Close-up view: 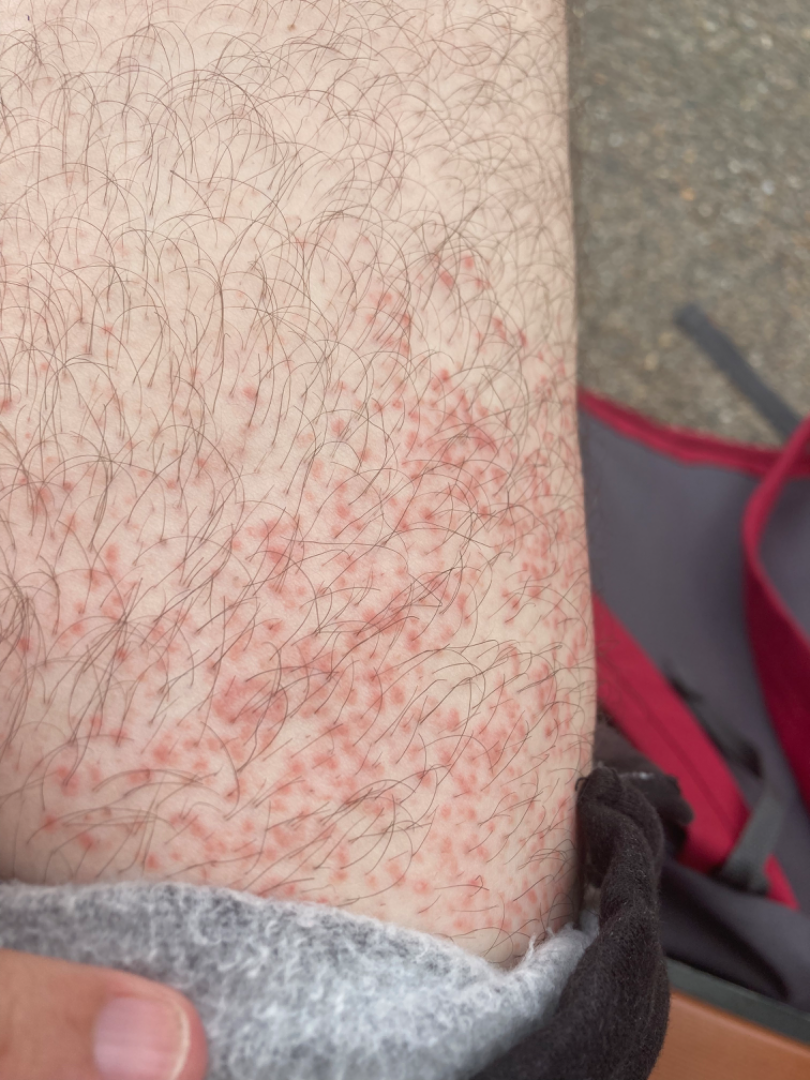{
  "differential": {
    "tied_lead": [
      "Folliculitis",
      "Keratosis pilaris"
    ],
    "unlikely": [
      "Miliaria"
    ]
  }
}